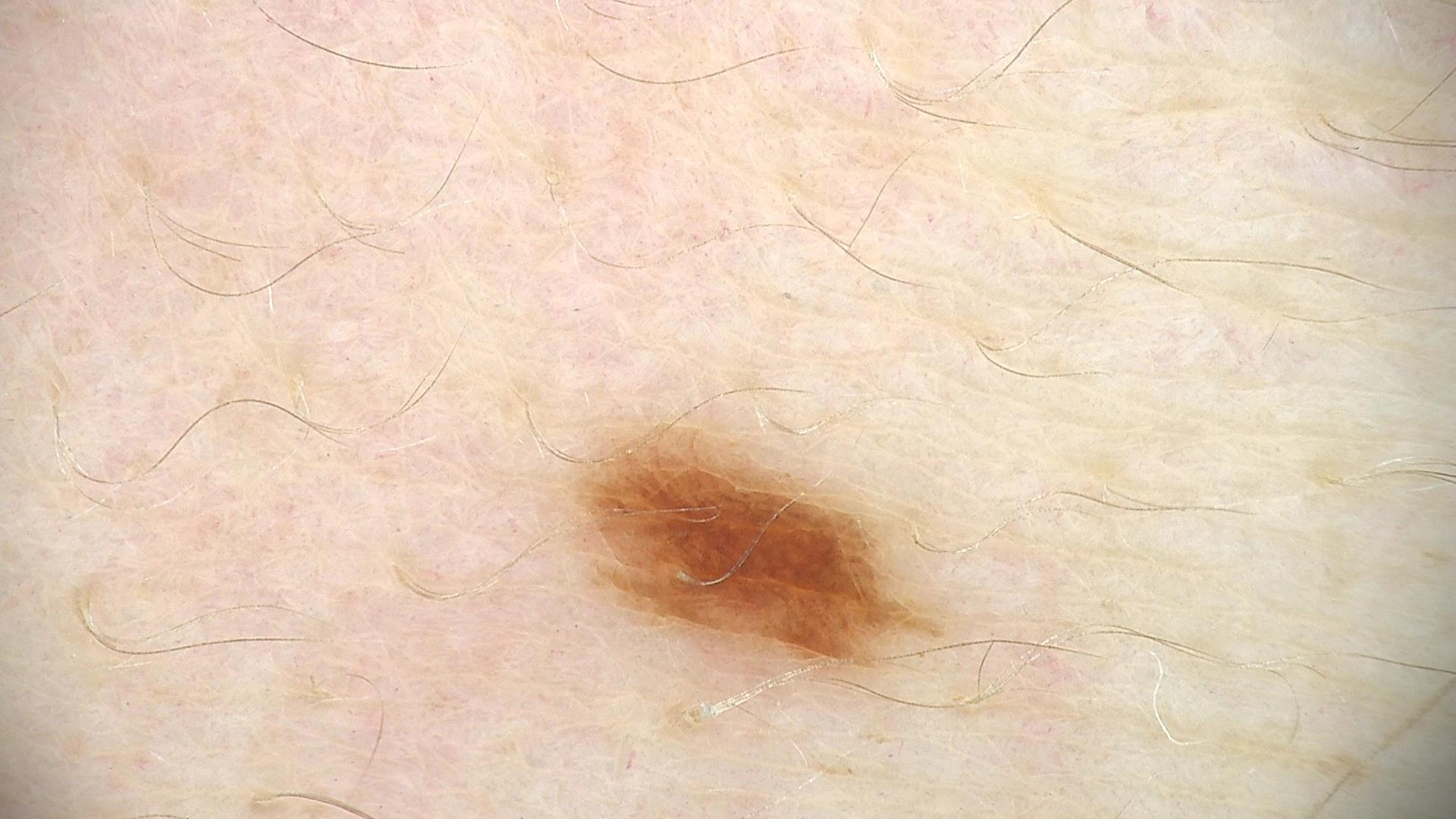<lesion>
<diagnosis>
<name>dysplastic junctional nevus</name>
<code>jd</code>
<malignancy>benign</malignancy>
<super_class>melanocytic</super_class>
<confirmation>expert consensus</confirmation>
</diagnosis>
</lesion>